Reported lesion symptoms include bothersome appearance, located on the leg, the patient reported no systemic symptoms, the condition has been present for less than one week, texture is reported as raised or bumpy, this is a close-up image: 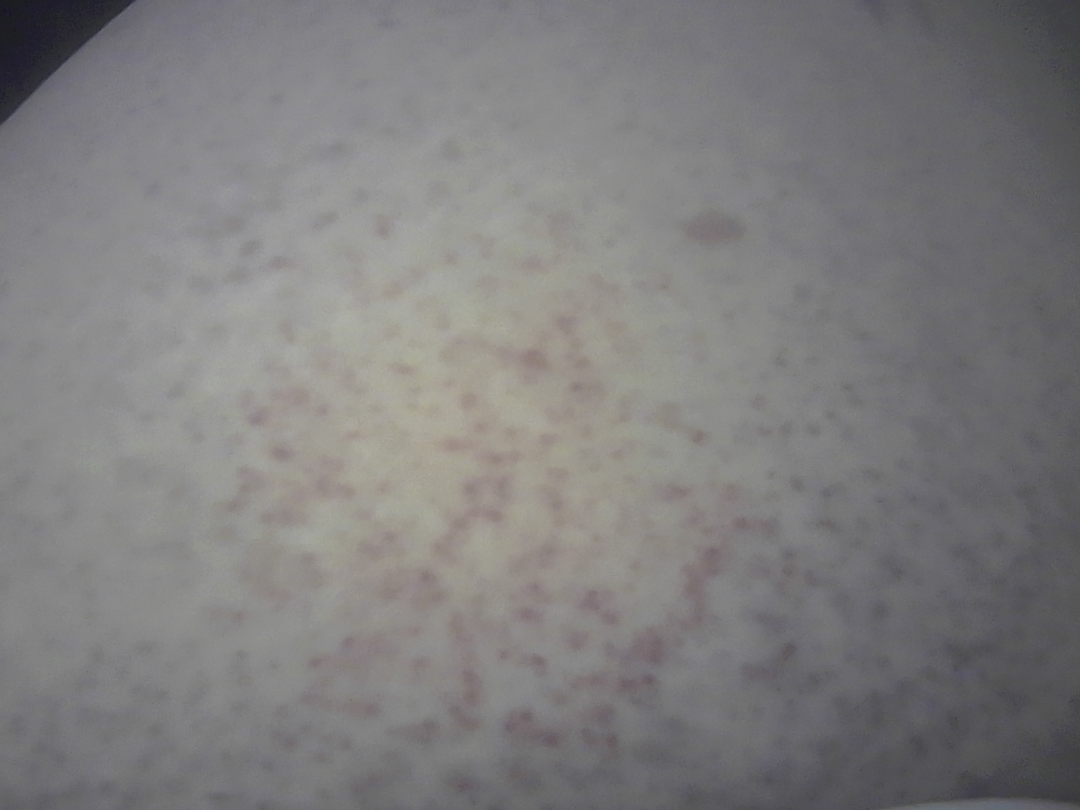| feature | finding |
|---|---|
| assessment | not assessable |